A male patient 62 years old · a smartphone photograph of a skin lesion:
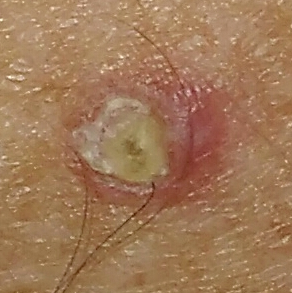Notes:
– location · a forearm
– pathology · actinic keratosis (biopsy-proven)